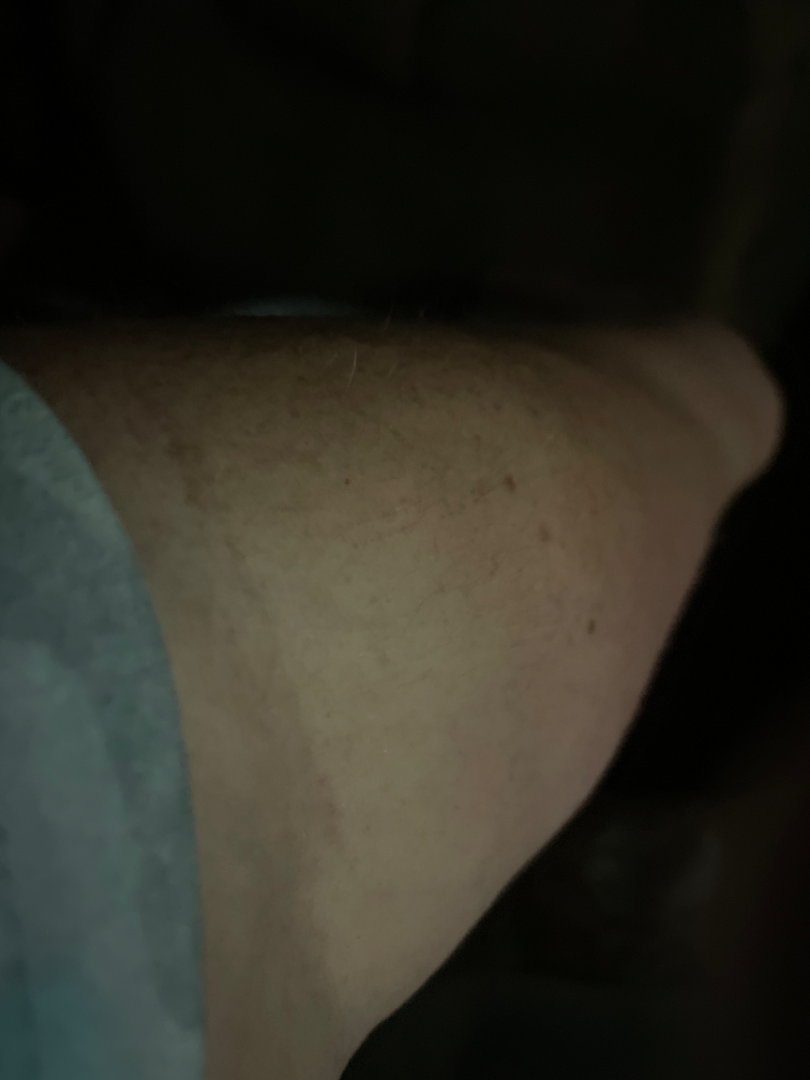The reviewer was unable to grade this case for skin condition. The patient considered this a rash. The lesion involves the leg, head or neck, back of the torso, arm and front of the torso. The lesion is associated with itching, burning and bothersome appearance. The photo was captured at a distance.